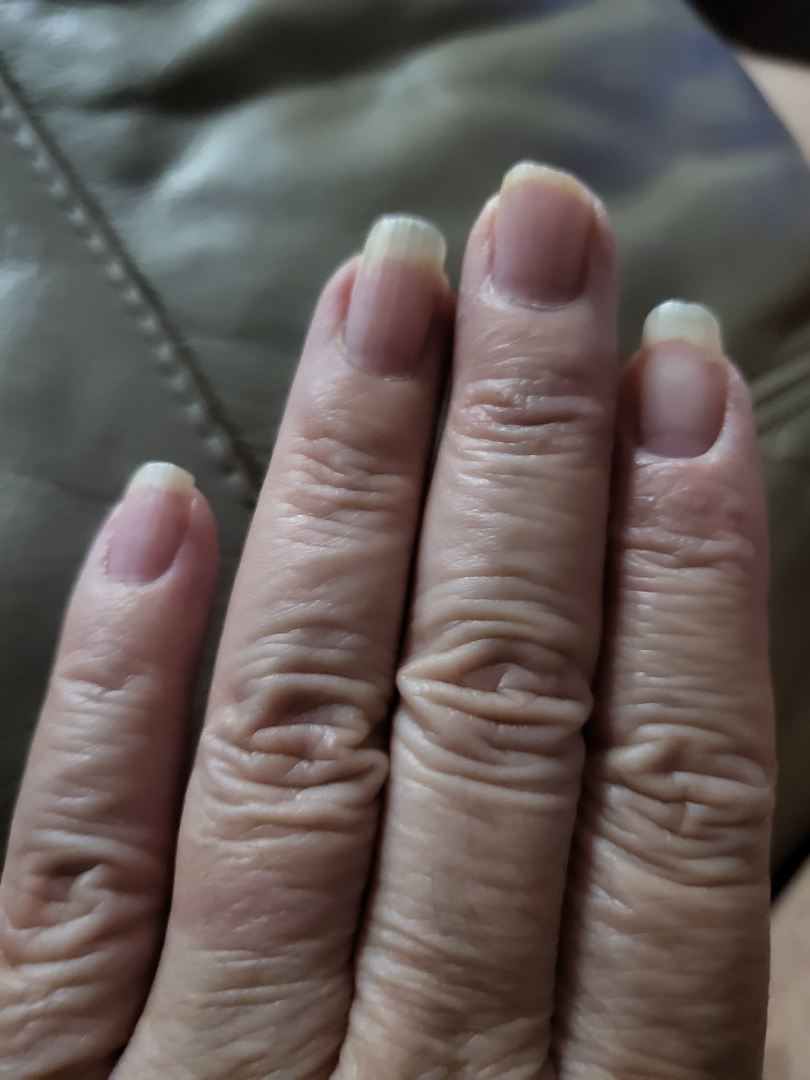The reviewing dermatologist did not identify a discernible skin condition.
Close-up view.
Self-categorized by the patient as a nail problem.
The affected area is the back of the hand and palm.
Reported duration is three to twelve months.